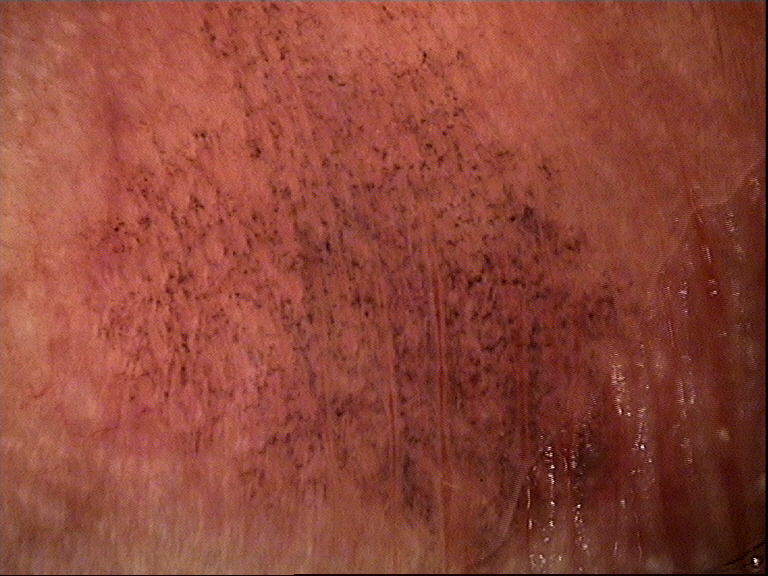A dermoscopy image of a single skin lesion. Classified as a benign lesion — an ink-spot lentigo.